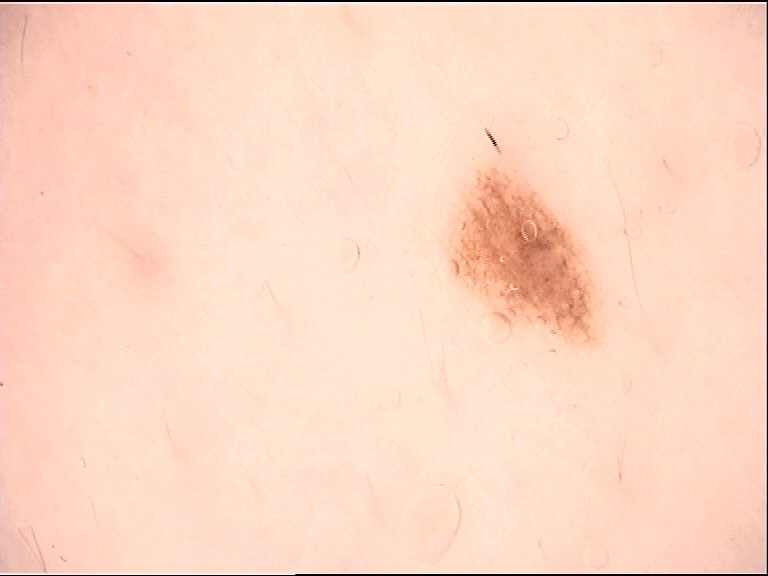Diagnosed as a benign lesion — a dysplastic junctional nevus.